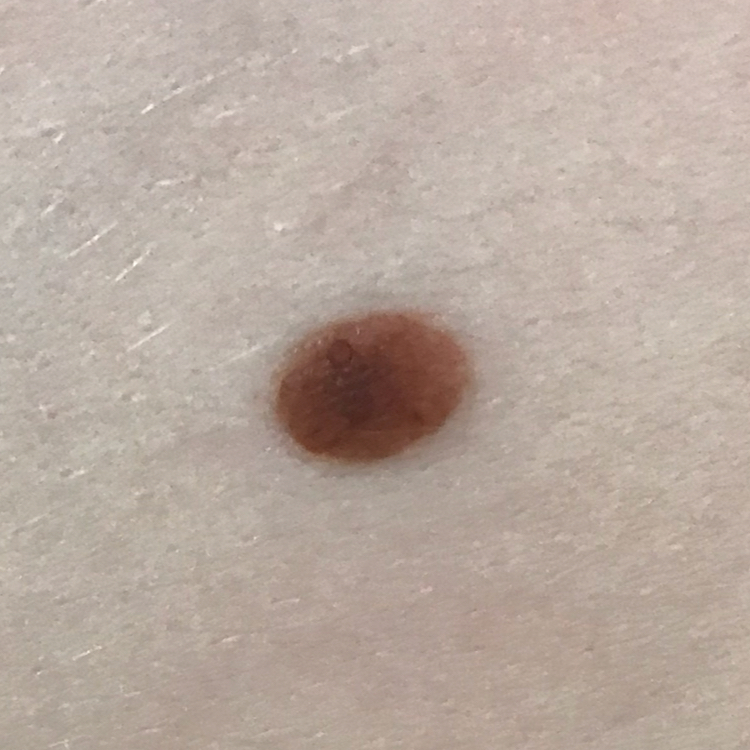{
  "diagnosis": {
    "name": "nevus",
    "code": "NEV",
    "malignancy": "benign",
    "confirmation": "clinical consensus"
  }
}